A female patient, aged approximately 60 · a dermoscopic view of a skin lesion: 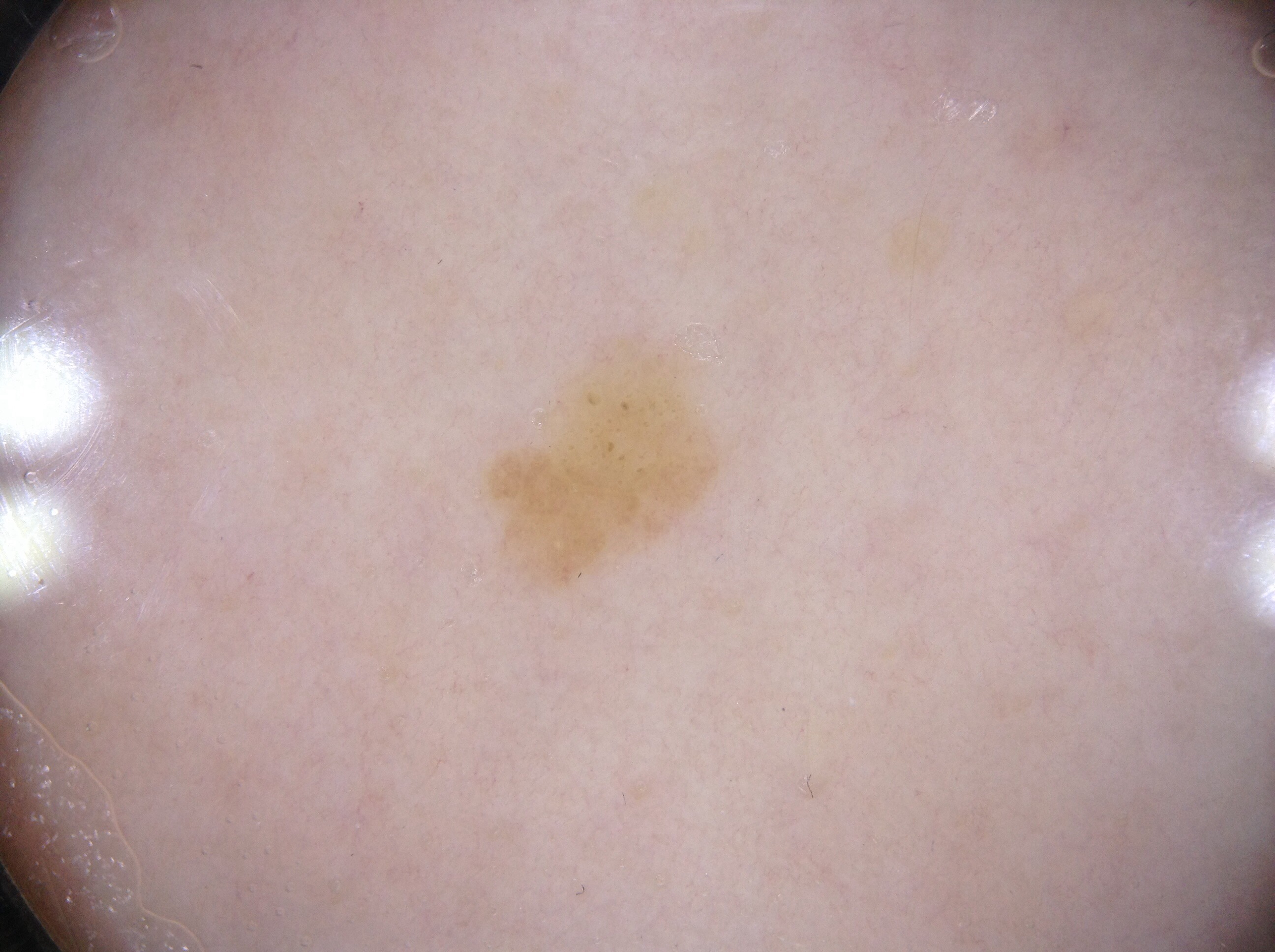Dermoscopic assessment notes no milia-like cysts, pigment network, negative network, or streaks. In (x1, y1, x2, y2) order, lesion location: [474,327,740,613]. Clinically diagnosed as a seborrheic keratosis.